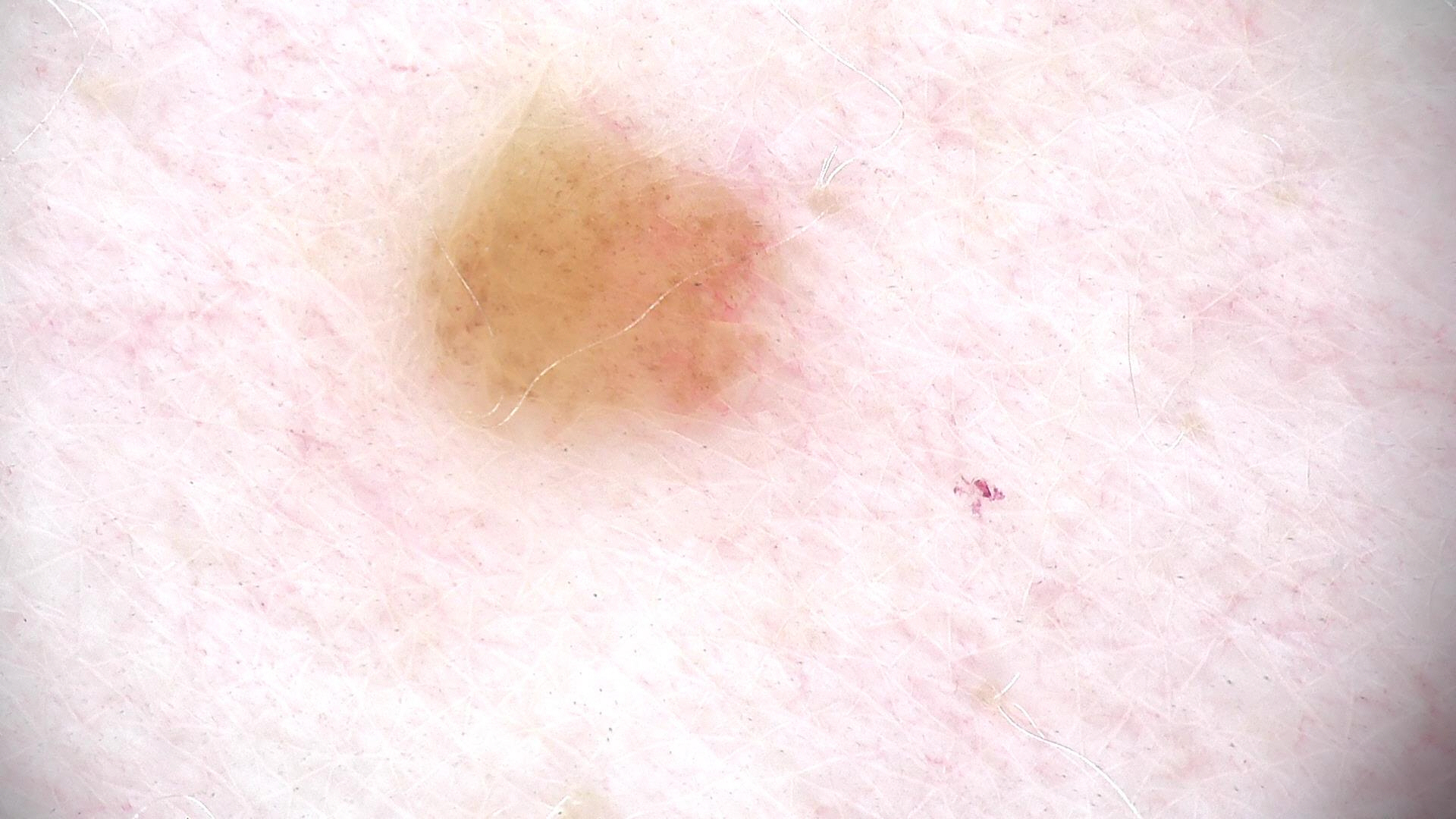Impression: Diagnosed as a banal lesion — a junctional nevus.